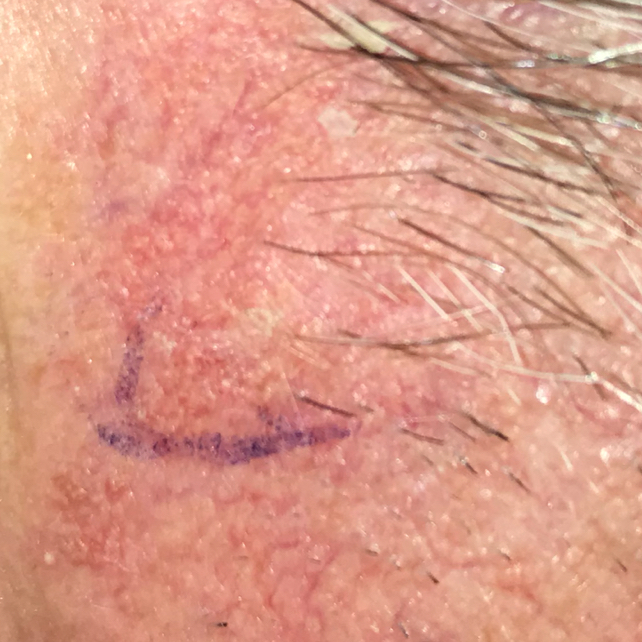The diagnostic impression was an actinic keratosis.